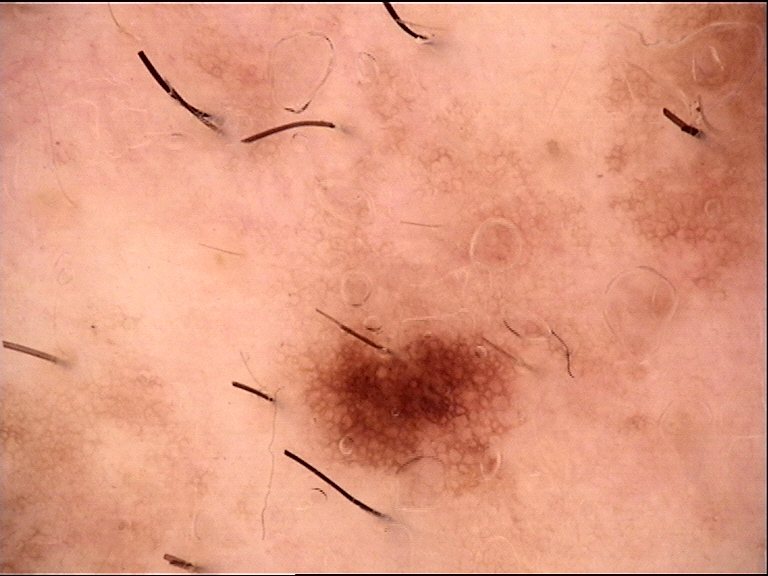{
  "diagnosis": {
    "name": "dysplastic junctional nevus",
    "code": "jd",
    "malignancy": "benign",
    "super_class": "melanocytic",
    "confirmation": "expert consensus"
  }
}